A clinical photograph showing a skin lesion; imaged for a research study, with no referral diagnosis recorded; a female patient 78 years of age.
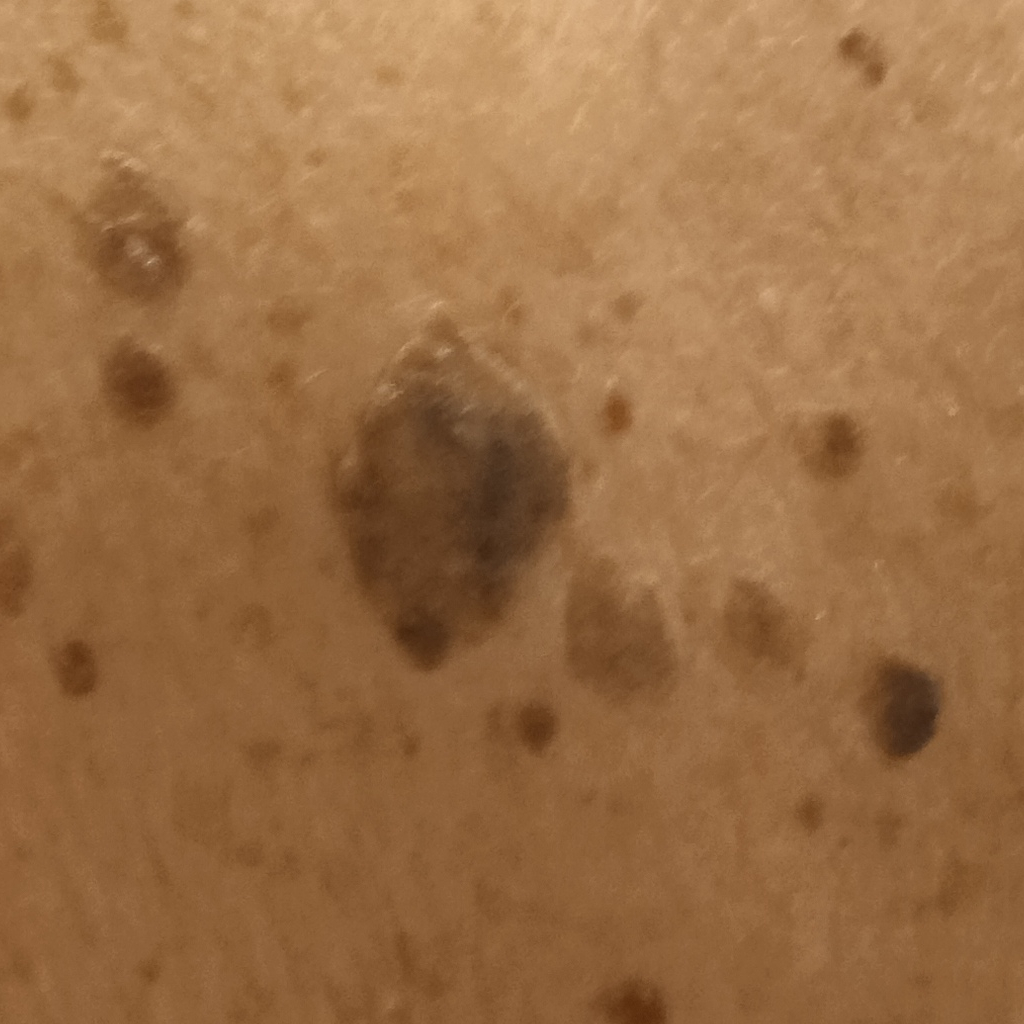Q: What is the anatomic site?
A: the back
Q: How large is the lesion?
A: 15.7 mm
Q: What was the diagnosis?
A: seborrheic keratosis (dermatologist consensus)